Close-up view. Located on the leg. Female contributor, age 18–29 — 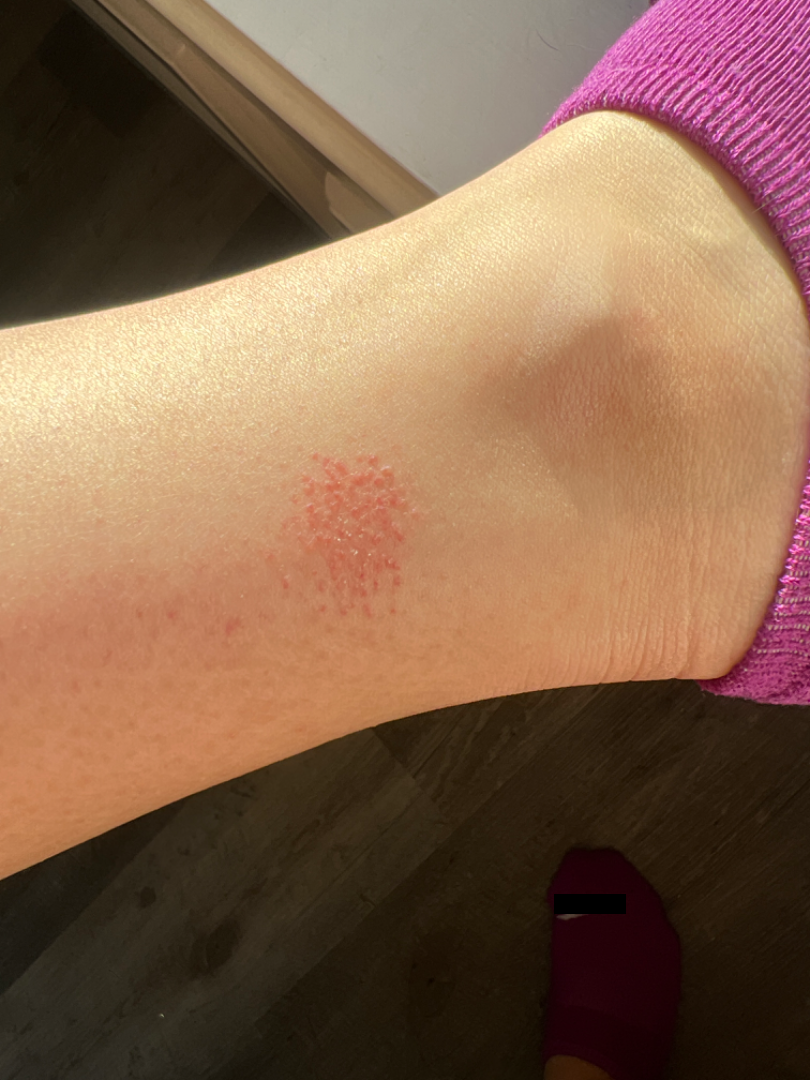Most likely Eczema.